A dermoscopic close-up of a skin lesion · a female patient, about 55 years old: 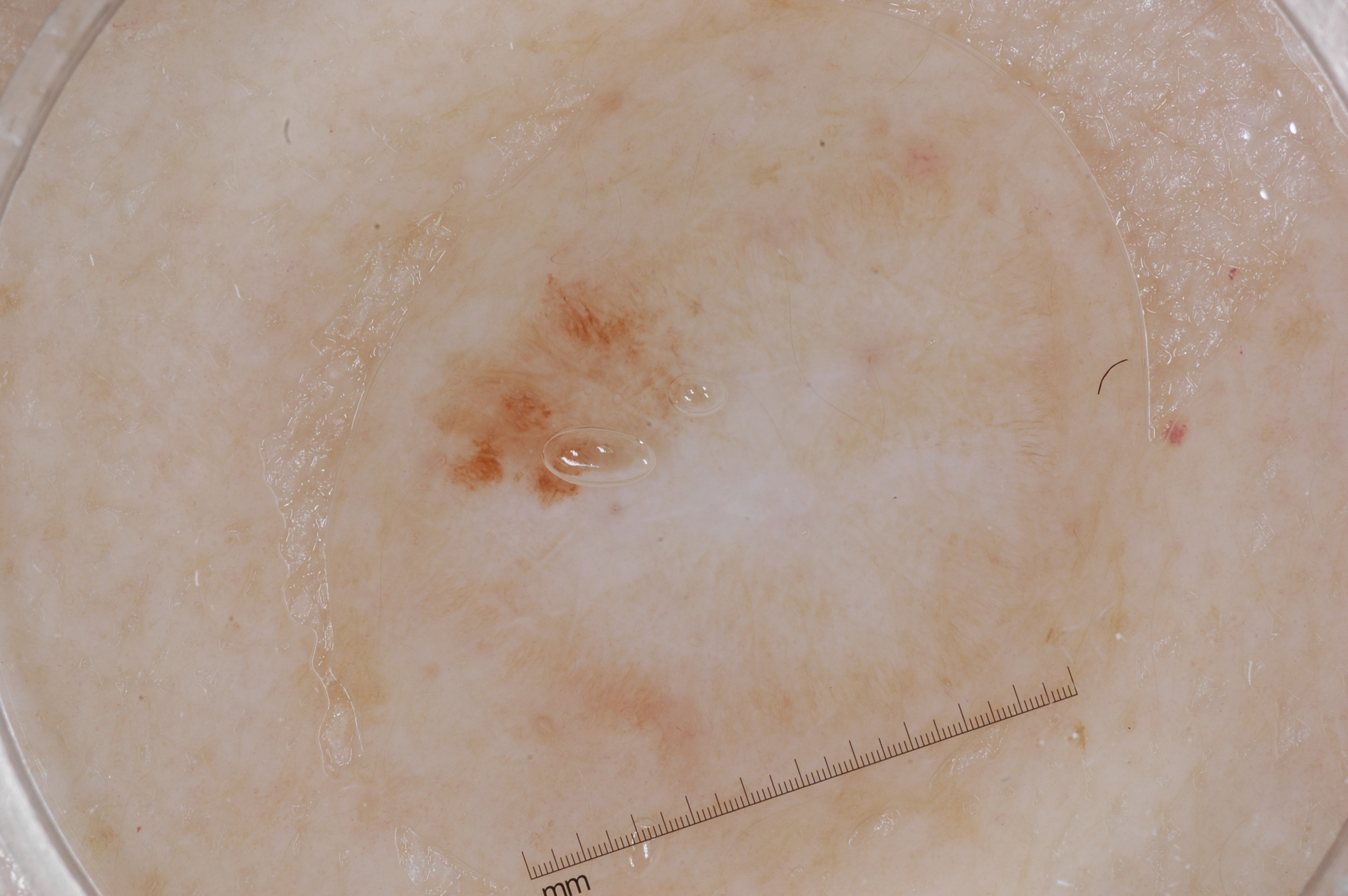Image and clinical context: The lesion takes up about 6% of the image. The lesion spans left=407, top=238, right=755, bottom=513. The dermoscopic pattern shows pigment network, with no negative network, streaks, or milia-like cysts. Conclusion: The clinical diagnosis was a melanocytic nevus.